The patient says their skin tans without first burning. A female patient age 92: 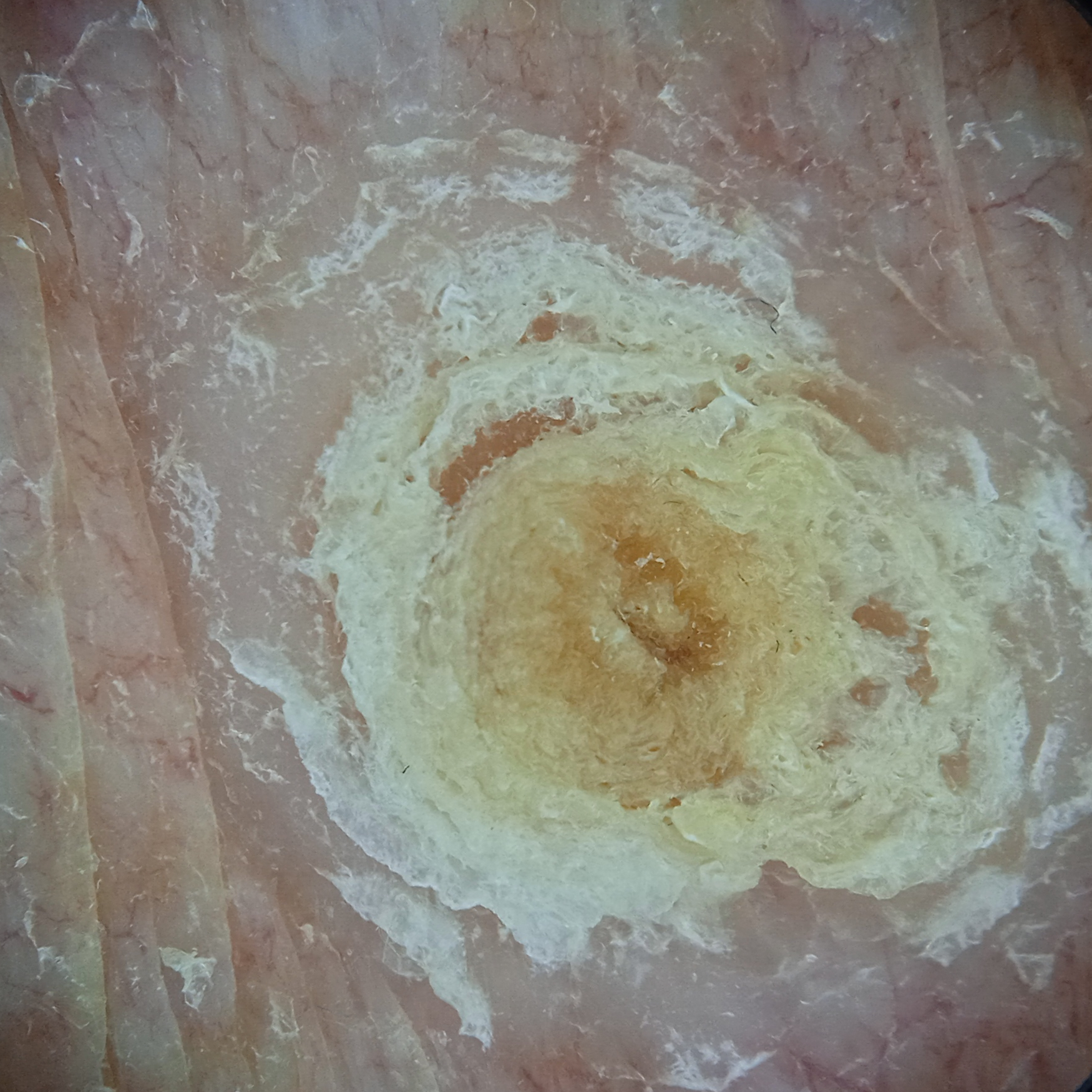Located on the torso.
The lesion measures approximately 12.5 mm.
The dermatologists' assessment was a squamous cell carcinoma.